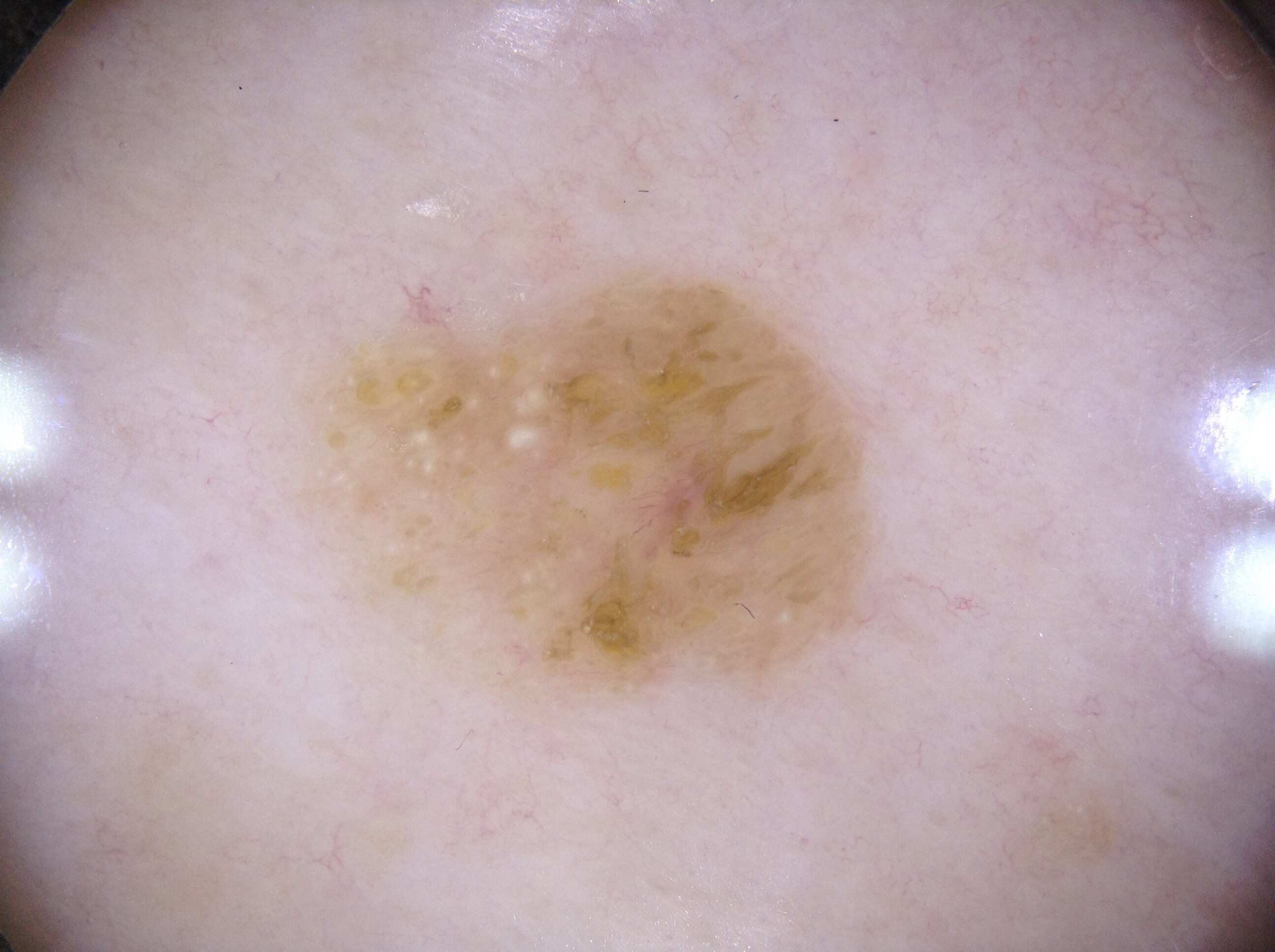Q: Patient demographics?
A: female, about 60 years old
Q: How was this image acquired?
A: dermoscopy of a skin lesion
Q: Which dermoscopic features were noted?
A: milia-like cysts
Q: How large is the lesion within the image?
A: moderate
Q: What is the lesion's bounding box?
A: (329, 275, 866, 684)
Q: What is the diagnosis?
A: a seborrheic keratosis, a benign skin lesion